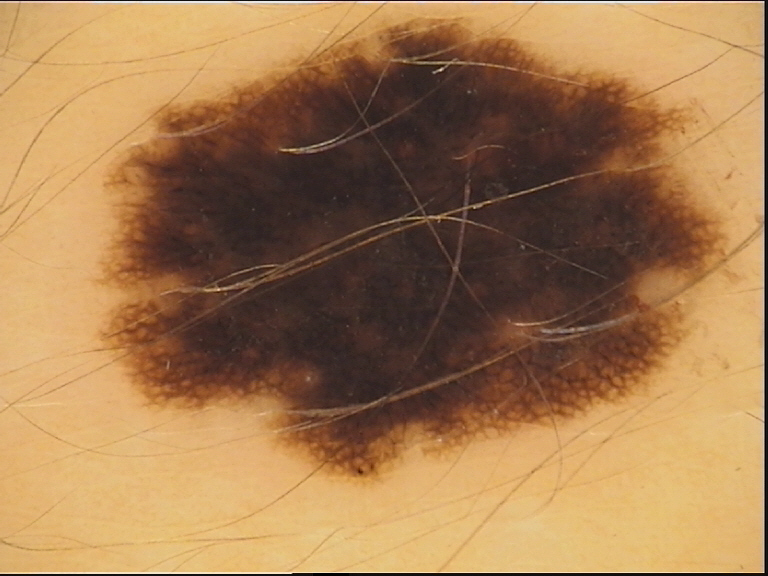The diagnostic label was a dysplastic compound nevus.